A dermoscopic photograph of a skin lesion.
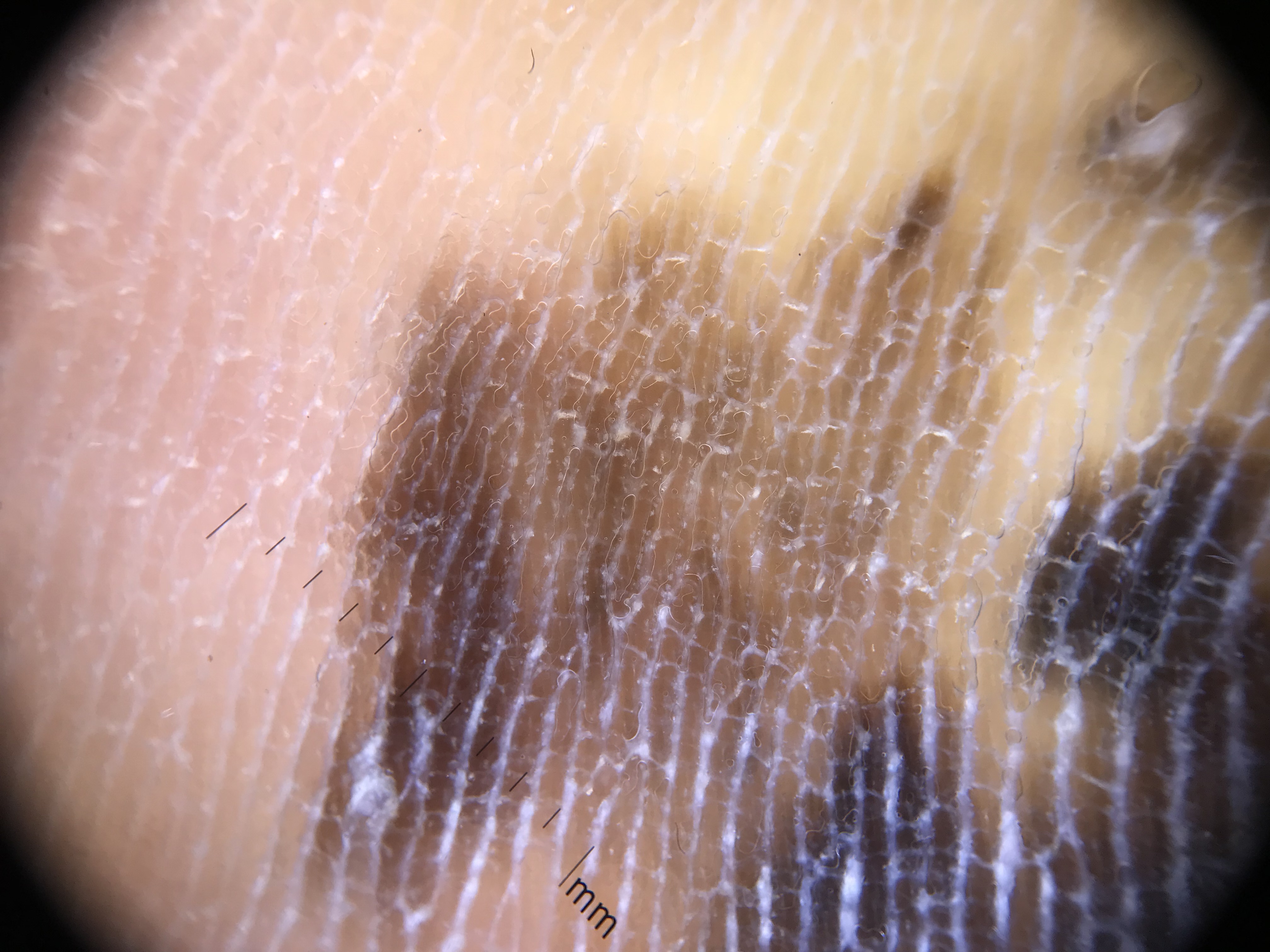Case:
- label: acral lentiginous melanoma (biopsy-proven)